A dermatoscopic image of a skin lesion · a female patient 60 years old · collected as part of a research study, without a referral diagnosis — 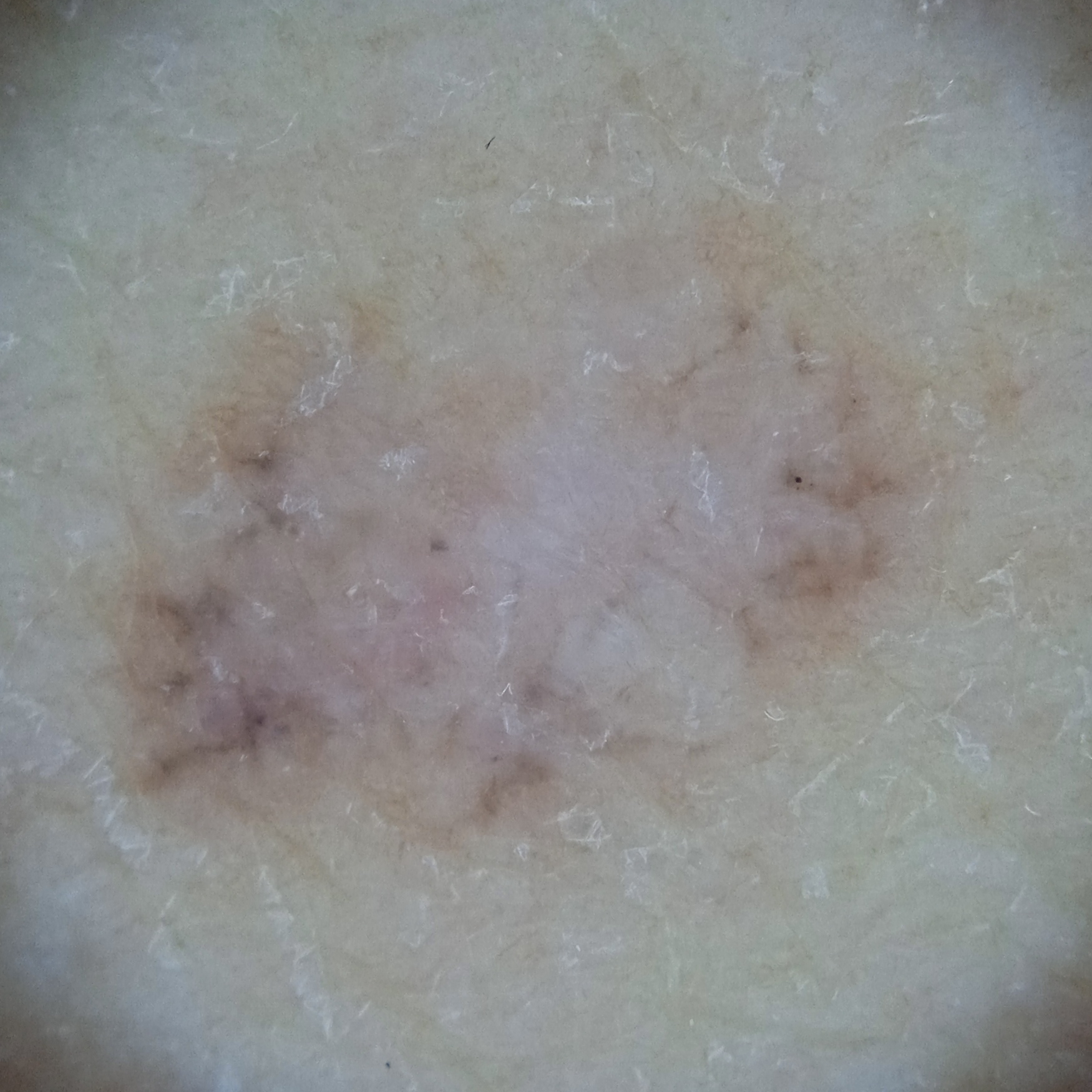location = the back; lesion size = 10.4 mm; diagnostic label = basal cell carcinoma (dermatologist consensus).